The patient is female; the photograph is a close-up of the affected area; the head or neck is involved — 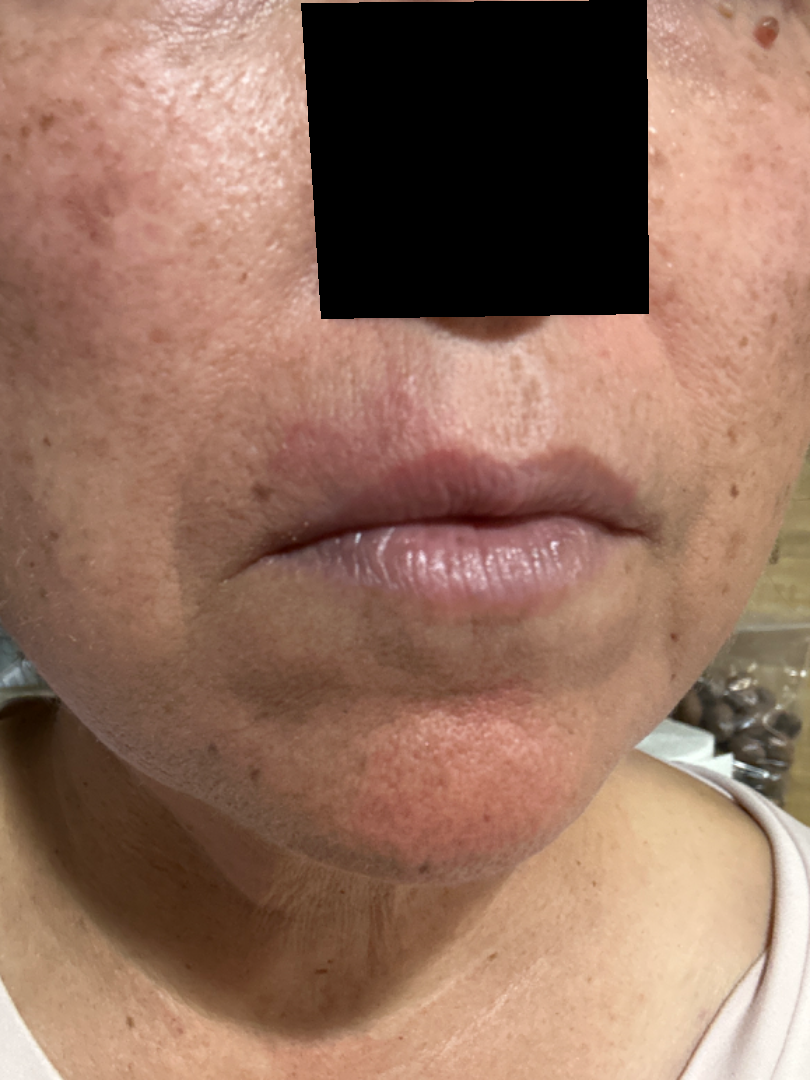On teledermatology review: the differential, in no particular order, includes Cutaneous lupus, Cutaneous sarcoidosis and Allergic Contact Dermatitis.